A dermoscopic close-up of a skin lesion; a female subject, approximately 30 years of age.
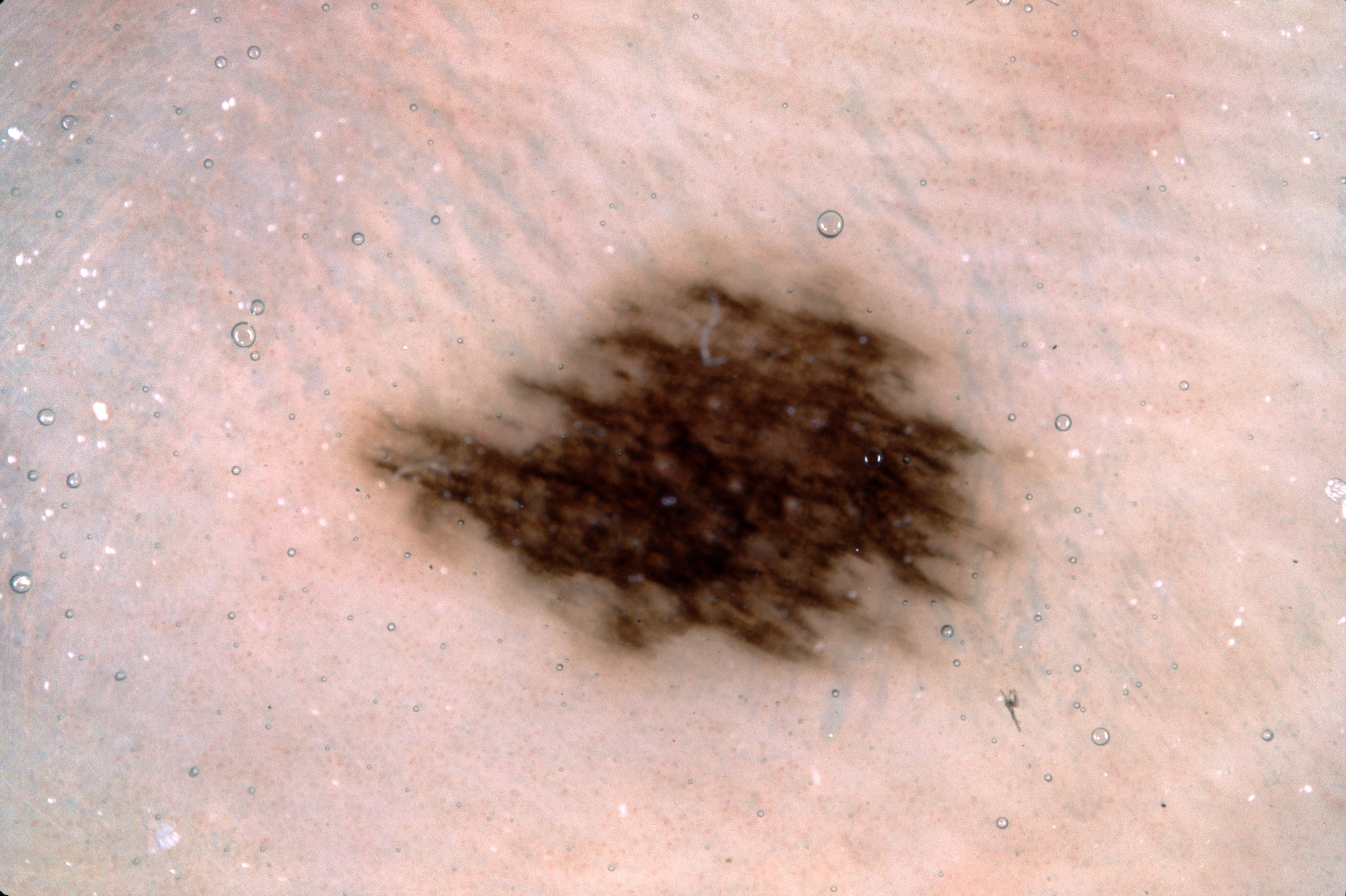| field | value |
|---|---|
| bounding box | left=353, top=242, right=1028, bottom=677 |
| lesion extent | ~15% of the field |
| dermoscopic pattern | pigment network |
| diagnosis | a melanocytic nevus |